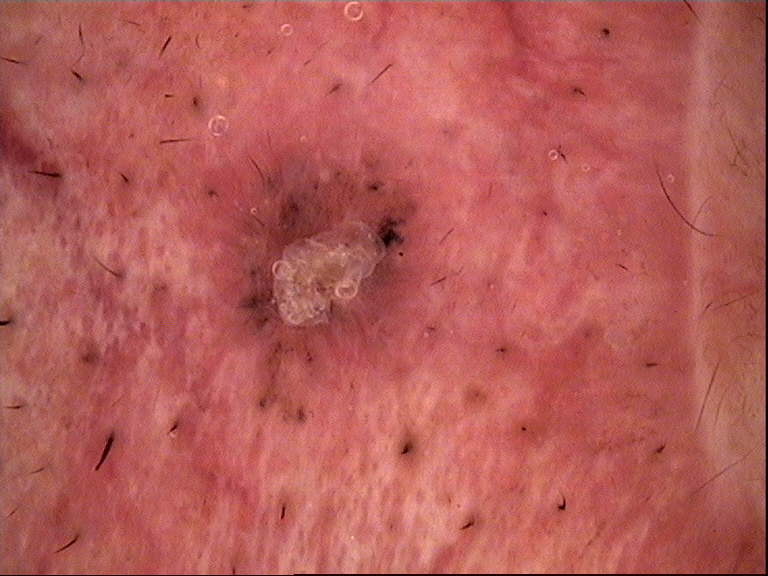This is a keratinocytic lesion.
Histopathologically confirmed as a basal cell carcinoma.